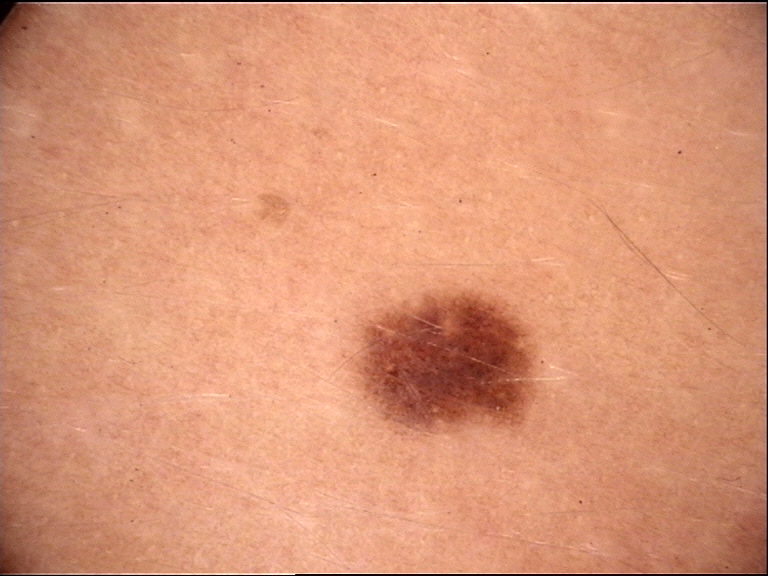Impression:
The diagnostic label was a dysplastic junctional nevus.